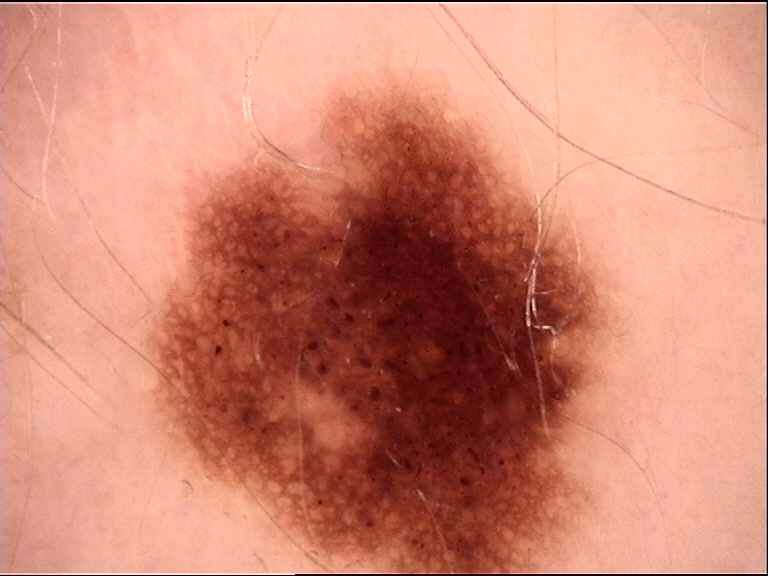modality: dermatoscopy; label: dysplastic junctional nevus (expert consensus).